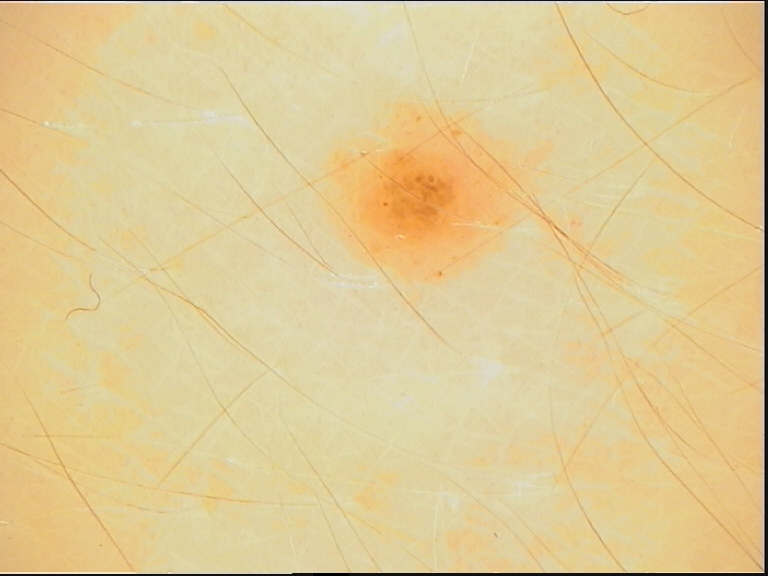Dermoscopy of a skin lesion. The diagnosis was a banal lesion — a junctional nevus.